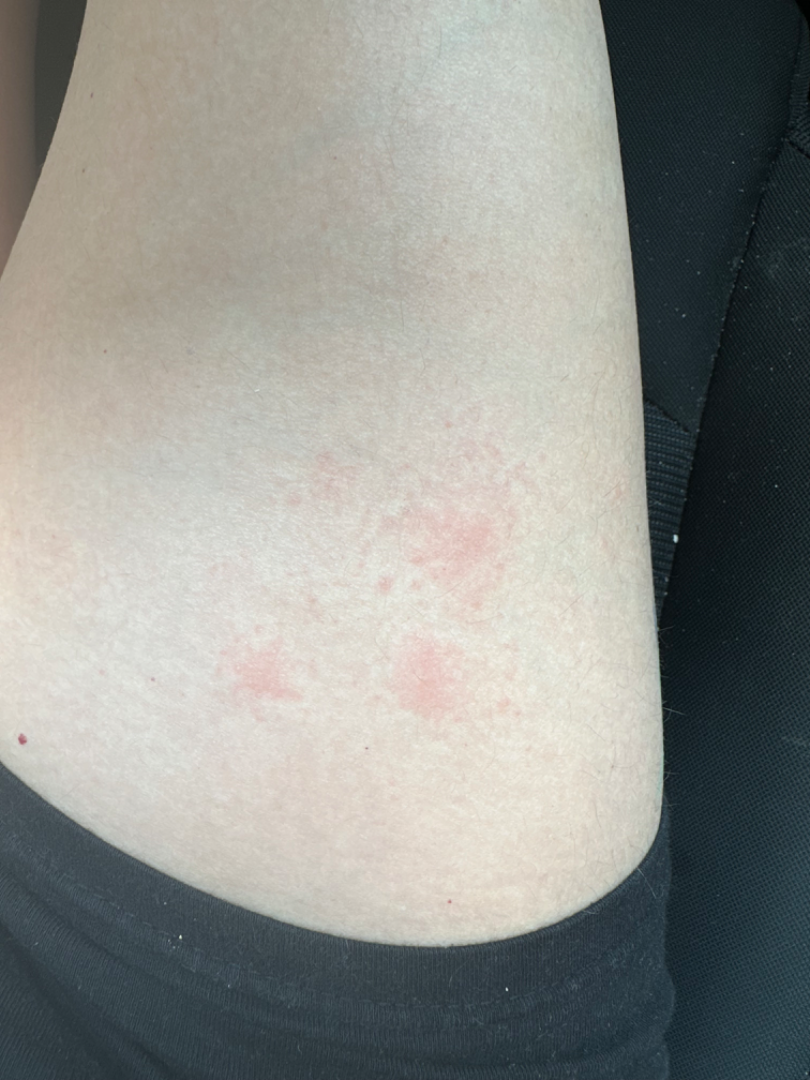The case was indeterminate on photographic review. The patient is a female aged 18–29. The affected area is the leg and arm. This is a close-up image.